A dermoscopy image of a single skin lesion, the patient is a male roughly 20 years of age: 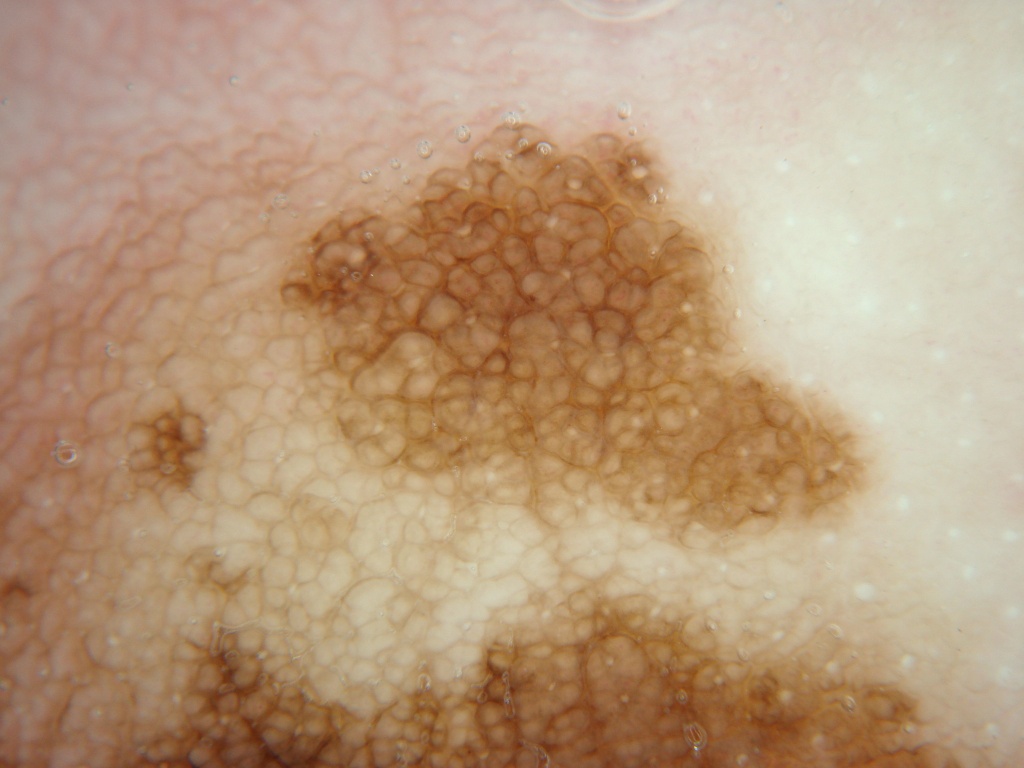extent = ~71% of the field | bounding box = 0, 73, 1018, 766 | lesion margin = reaches the image border | dermoscopic features = pigment network and milia-like cysts; absent: globules, negative network, and streaks | impression = a melanocytic nevus.